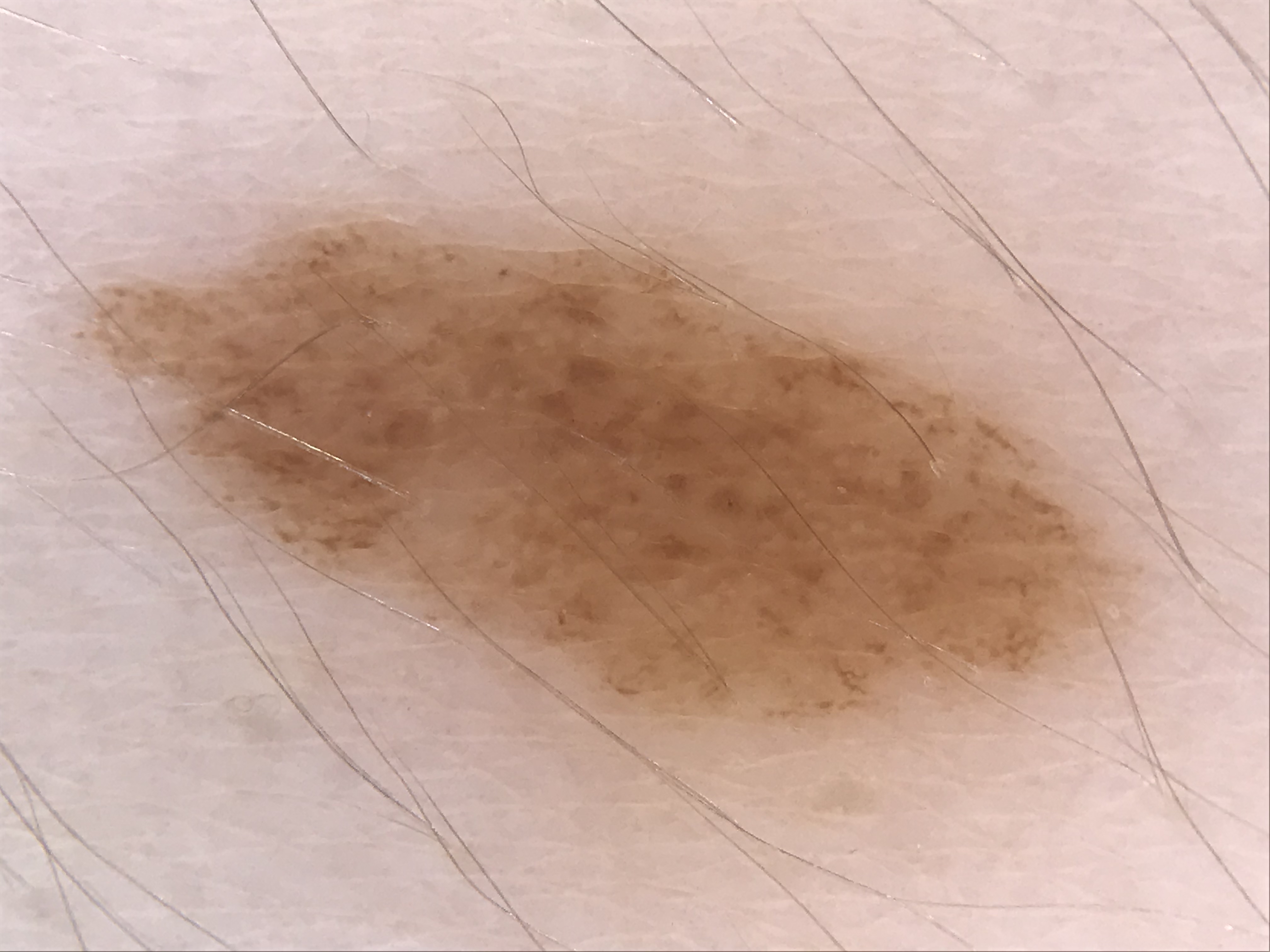diagnostic label = dysplastic junctional nevus (expert consensus)